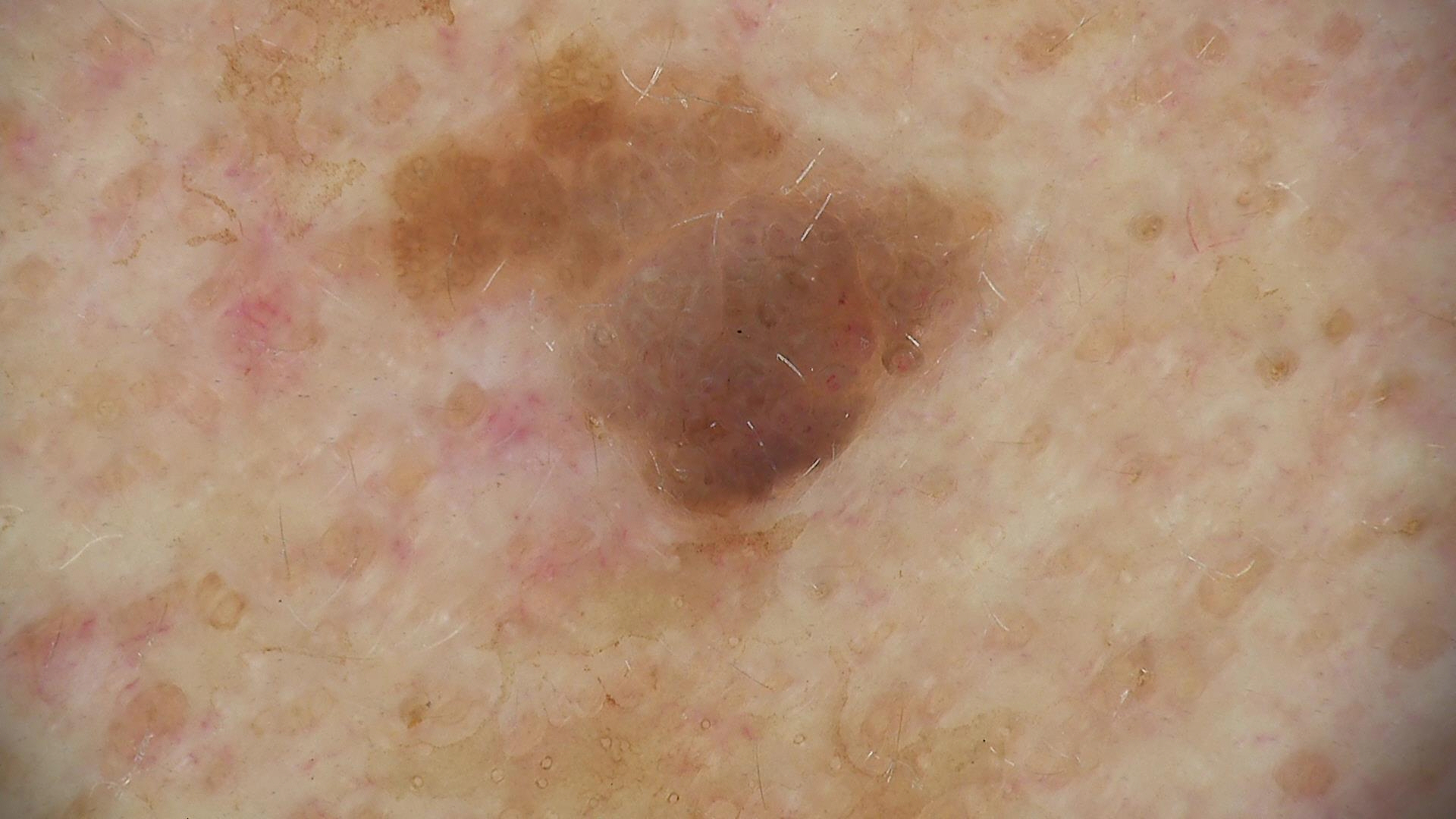Findings:
Dermoscopy of a skin lesion.
Conclusion:
Labeled as a keratinocytic lesion — a seborrheic keratosis.